A clinical photo of a skin lesion taken with a smartphone · a subject in their early 60s — 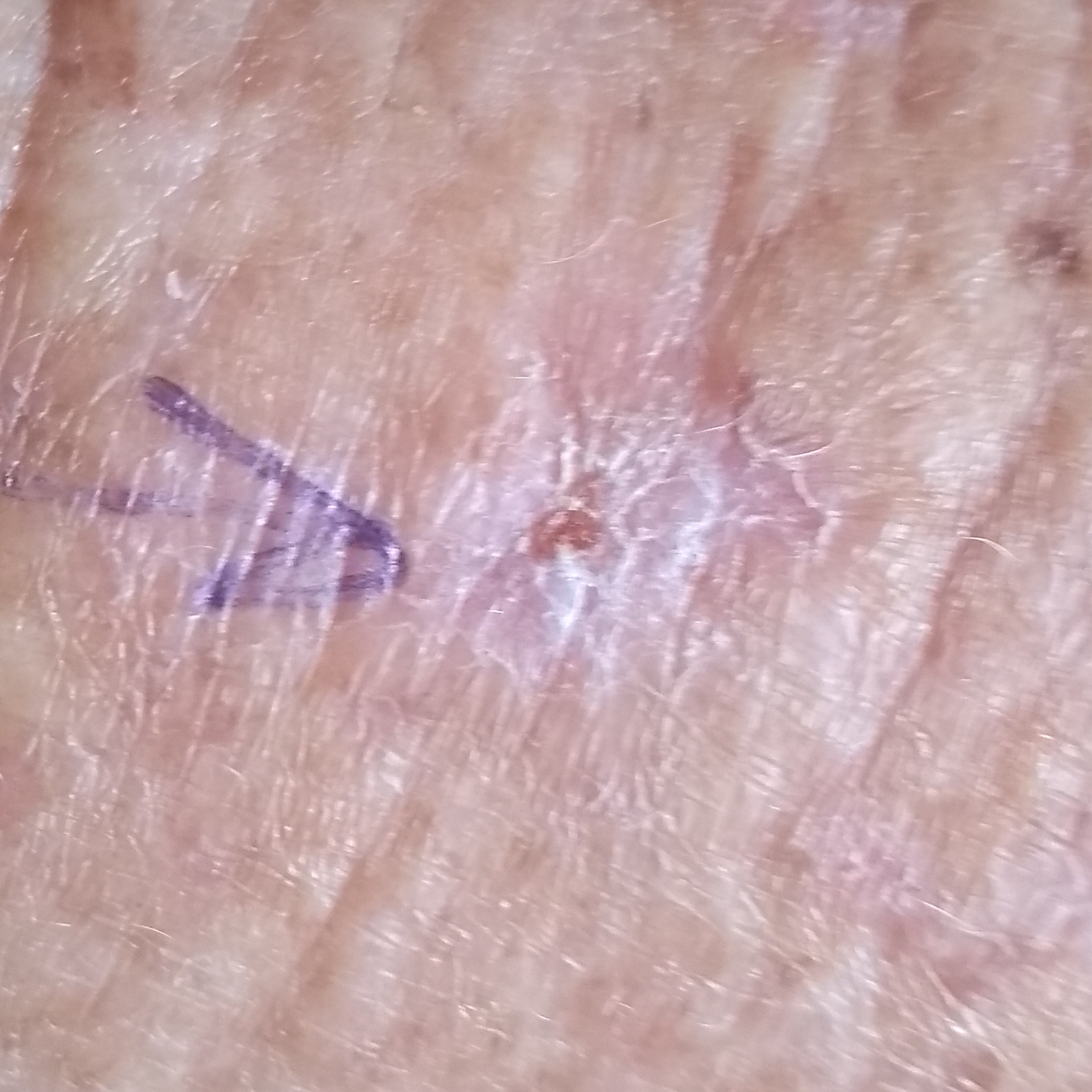Q: What is the anatomic site?
A: a forearm
Q: What symptoms does the patient report?
A: none reported
Q: What was the clinical impression?
A: actinic keratosis (clinical consensus)